The photo was captured at an angle · the lesion involves the top or side of the foot, back of the hand, arm, leg and front of the torso · the patient is a female aged 18–29.
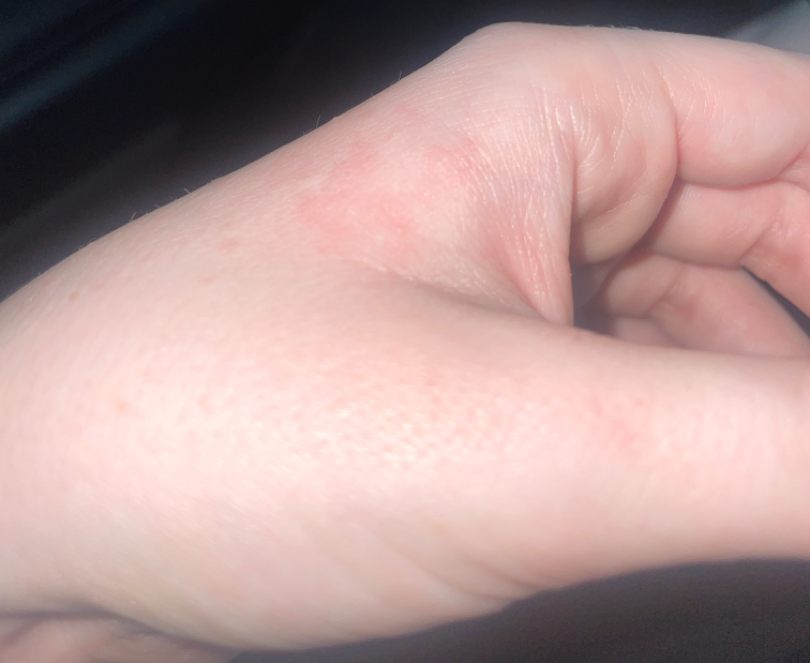Patient information:
No relevant systemic symptoms. Self-categorized by the patient as a rash. The lesion is described as raised or bumpy. Reported duration is one to four weeks.
Review:
On independent review by the dermatologists, the leading consideration is Eczema; also on the differential is Irritant Contact Dermatitis; less likely is Lichen planus/lichenoid eruption; less probable is Allergic Contact Dermatitis.